A male subject, about 60 years old · a skin lesion imaged with a dermatoscope:
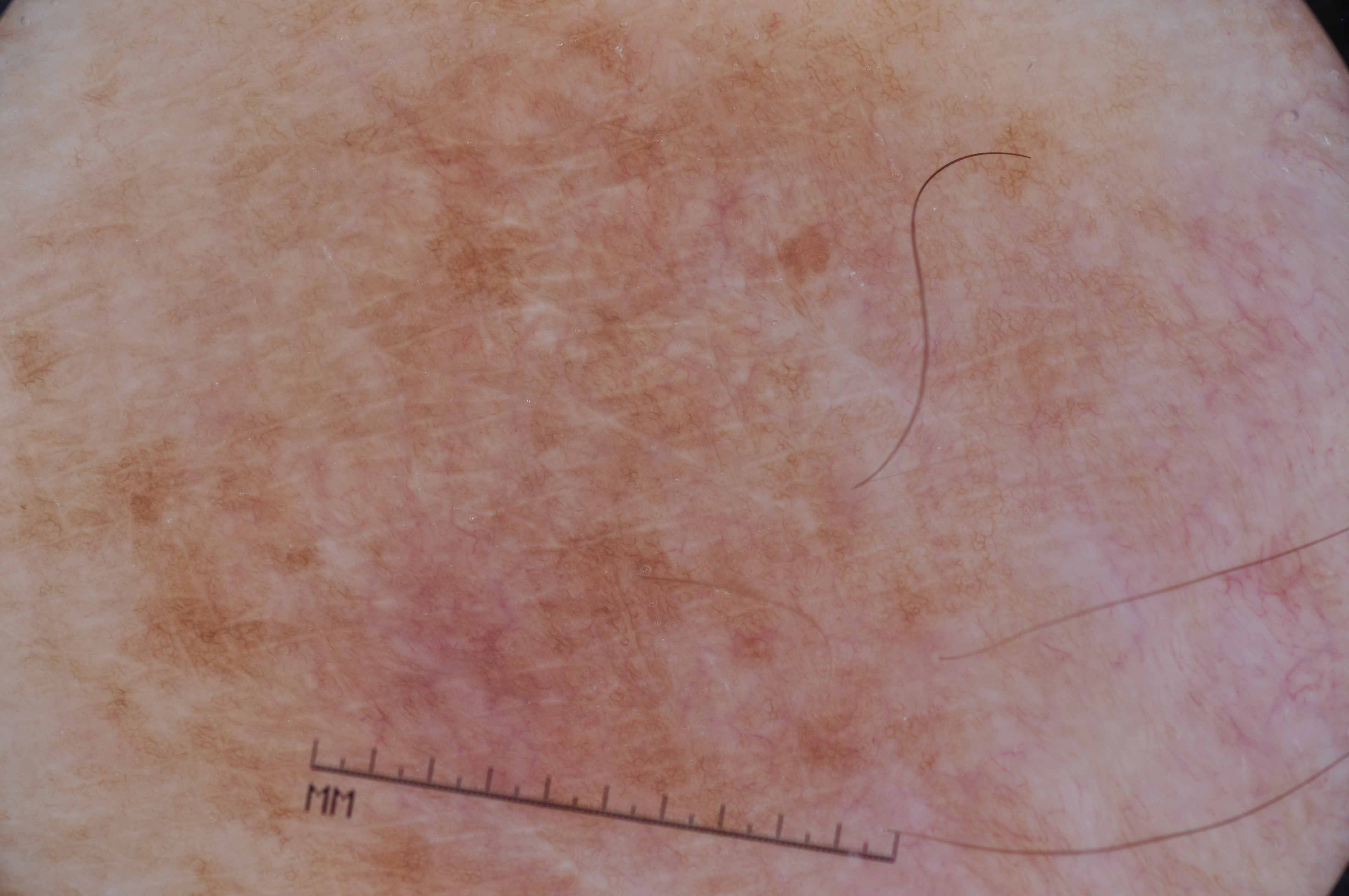The lesion reaches across nearly the entire image.
Dermoscopic review identifies pigment network.
Diagnosed as a seborrheic keratosis, a benign lesion.